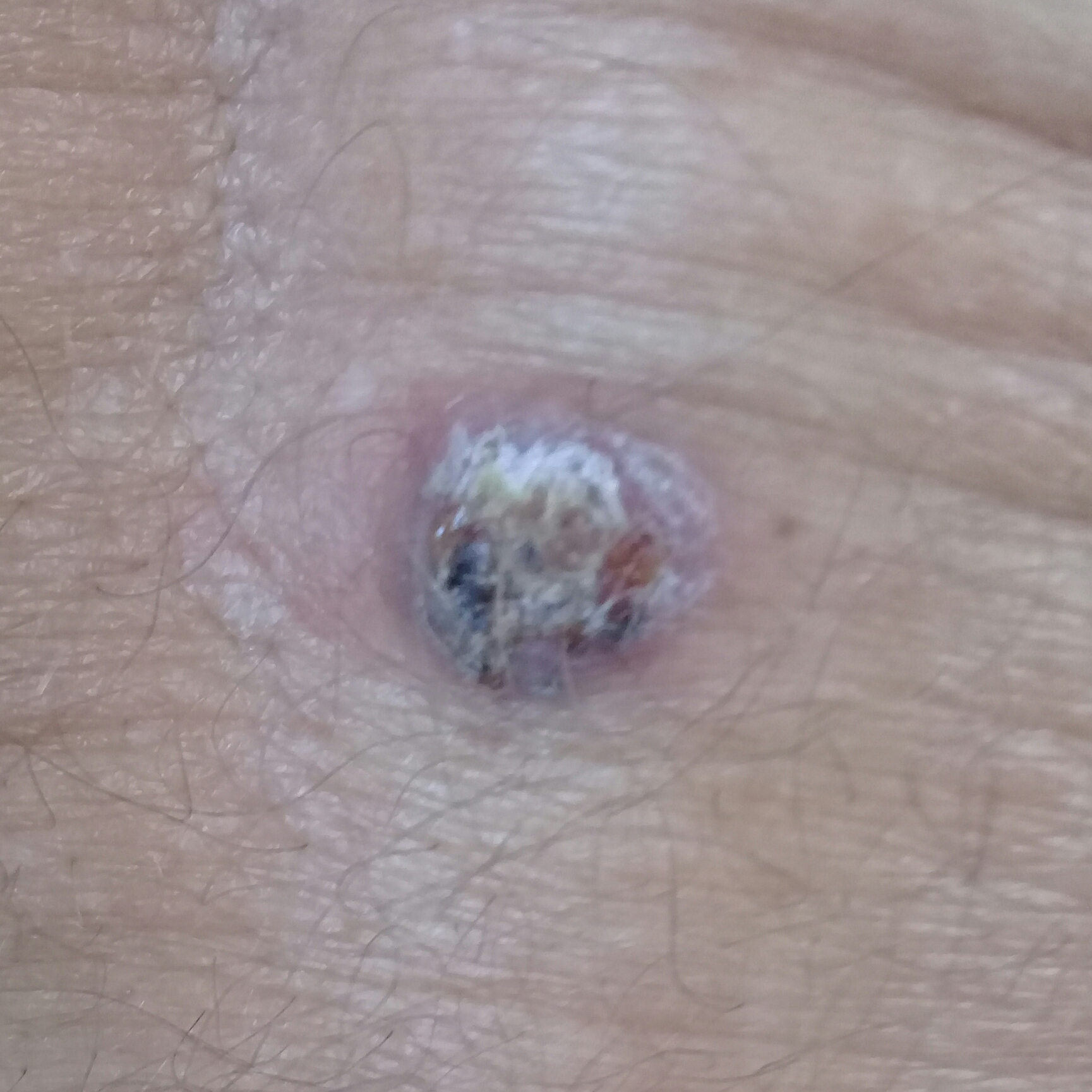  image: clinical photograph
  patient:
    age: 69
    gender: male
  lesion_location: the back
  symptoms:
    present:
      - itching
      - elevation
  diagnosis:
    name: basal cell carcinoma
    code: BCC
    malignancy: malignant
    confirmation: histopathology